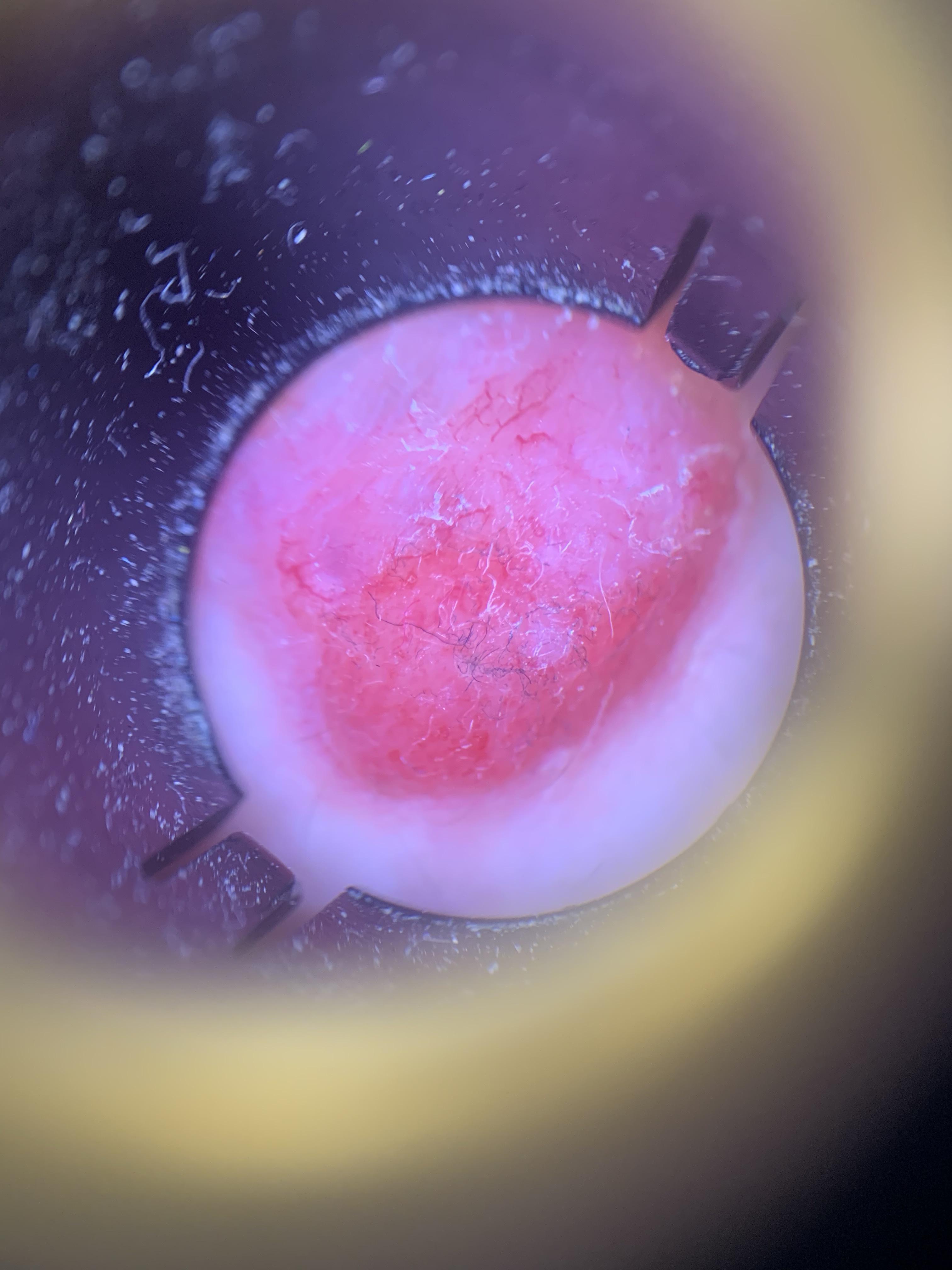Q: What kind of image is this?
A: contact-polarized dermoscopy
Q: Skin phototype?
A: II
Q: Where on the body is the lesion?
A: the anterior trunk
Q: What did the workup show?
A: Basal cell carcinoma (biopsy-proven)